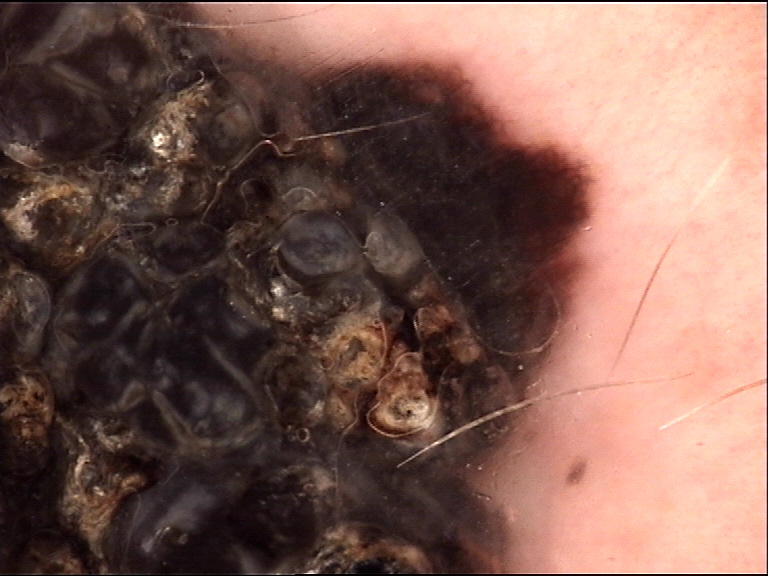A dermoscopic close-up of a skin lesion.
Histopathologically confirmed as a skin cancer — a melanoma.